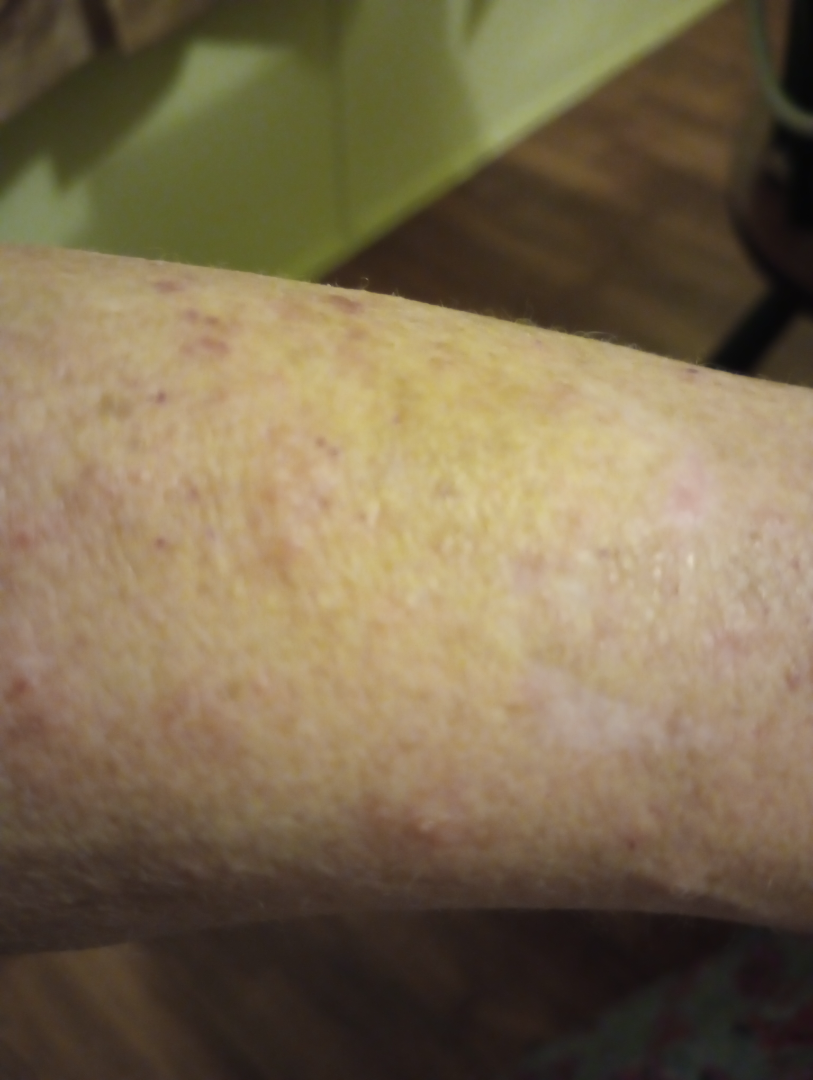Case summary:
– surface texture — raised or bumpy
– lesion symptoms — itching
– other reported symptoms — none reported
– image framing — close-up
– present for — about one day
– patient describes the issue as — a rash
– location — arm